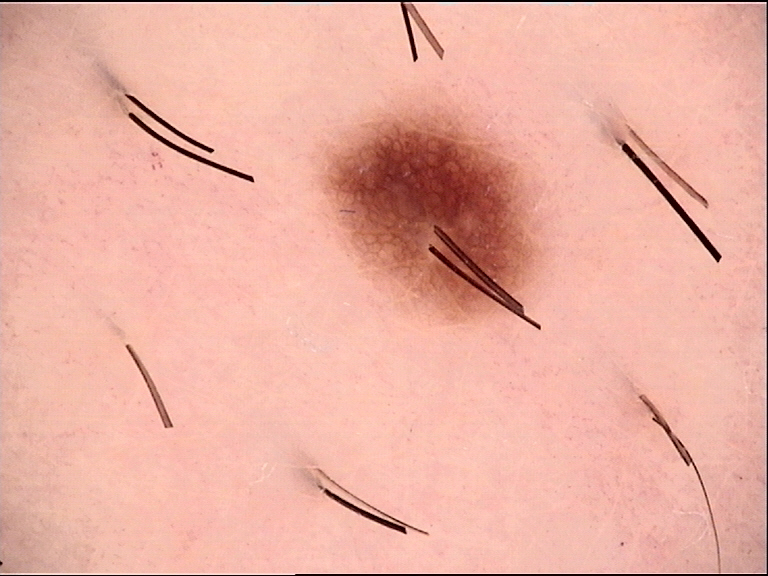modality: dermatoscopy
diagnostic label: dysplastic junctional nevus (expert consensus)